A dermoscopic image of a skin lesion.
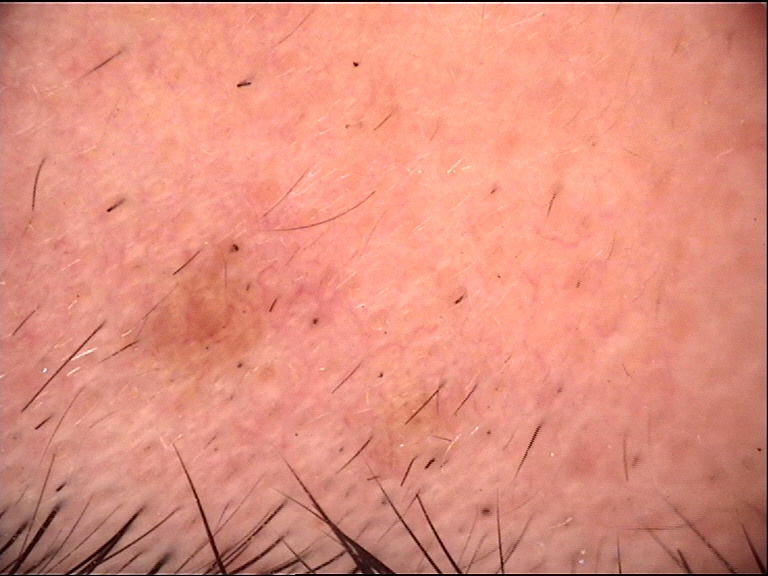Classified as a compound lesion — a Miescher nevus.